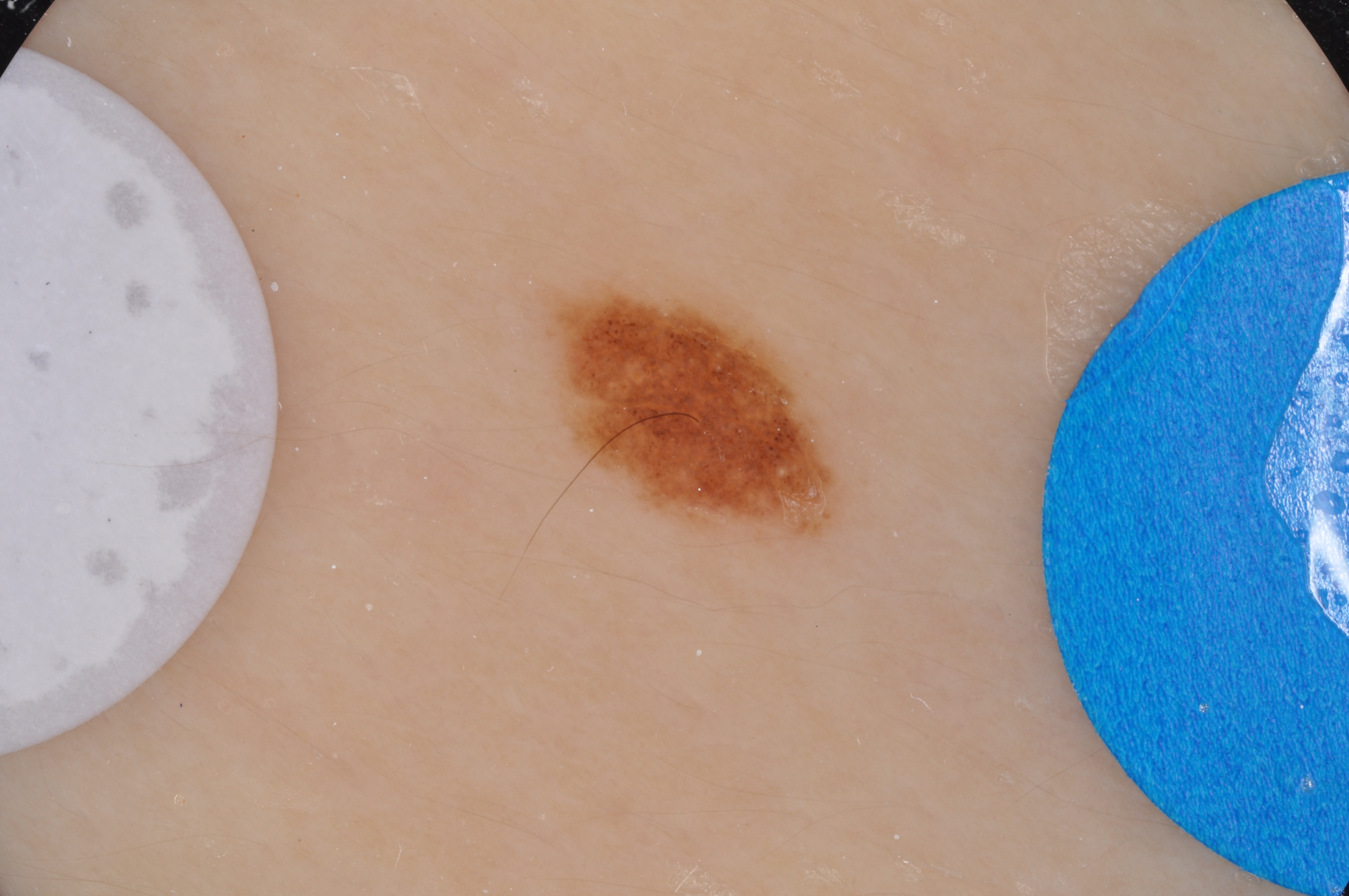subject=female, aged around 15
modality=dermoscopy
dermoscopic findings=globules and milia-like cysts; absent: pigment network, streaks, and negative network
lesion location=545, 285, 840, 543
impression=a melanocytic nevus, a benign skin lesion